The contributor is a male aged 30–39; the lesion involves the arm; the photograph was taken at a distance:
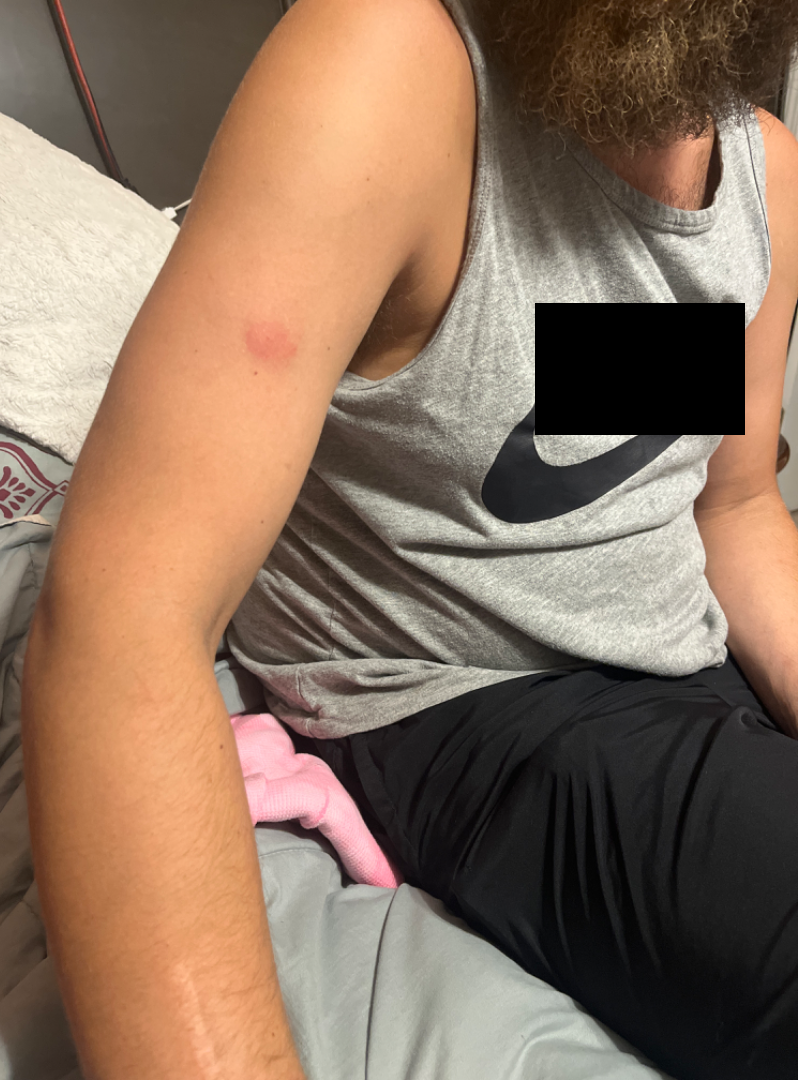The skin condition could not be confidently assessed from this image.